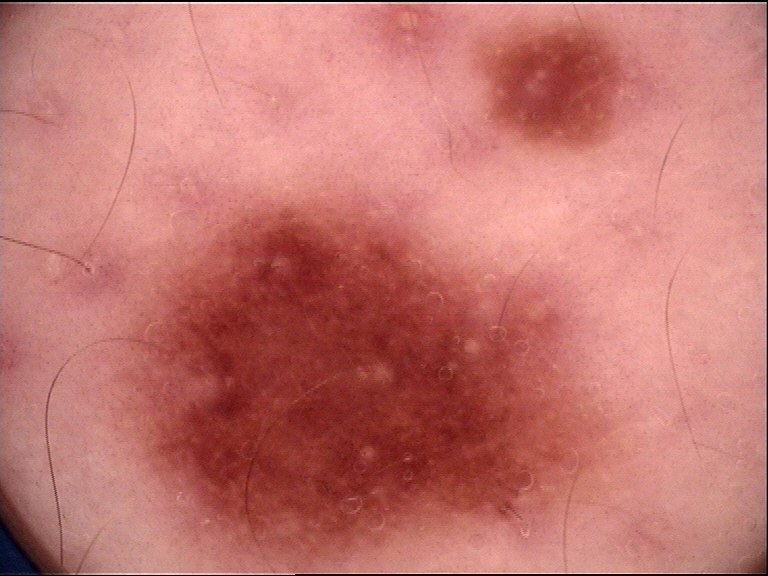Impression: The diagnosis was a benign lesion — a dysplastic junctional nevus.